The photo was captured at an angle; the patient indicates the lesion is raised or bumpy; present for less than one week; located on the arm; symptoms reported: pain, itching and burning; self-categorized by the patient as skin that appeared healthy to them; male contributor, age 30–39.
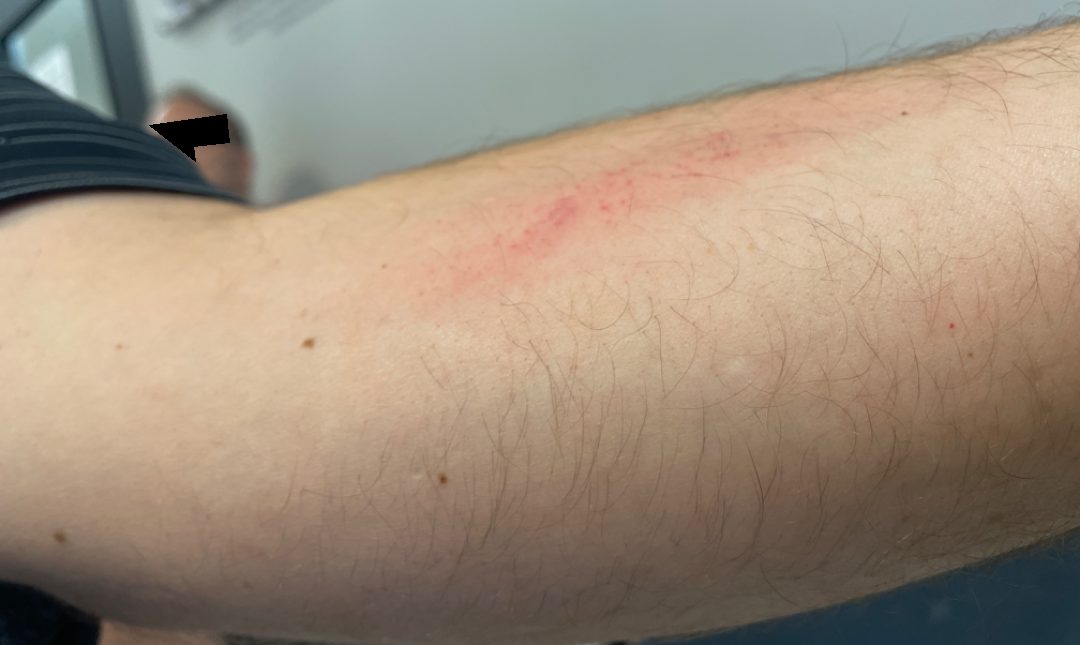Diagnostic features were not clearly distinguishable in this photograph.